The lesion involves the leg. The subject is 40–49, male. The photo was captured at an angle.
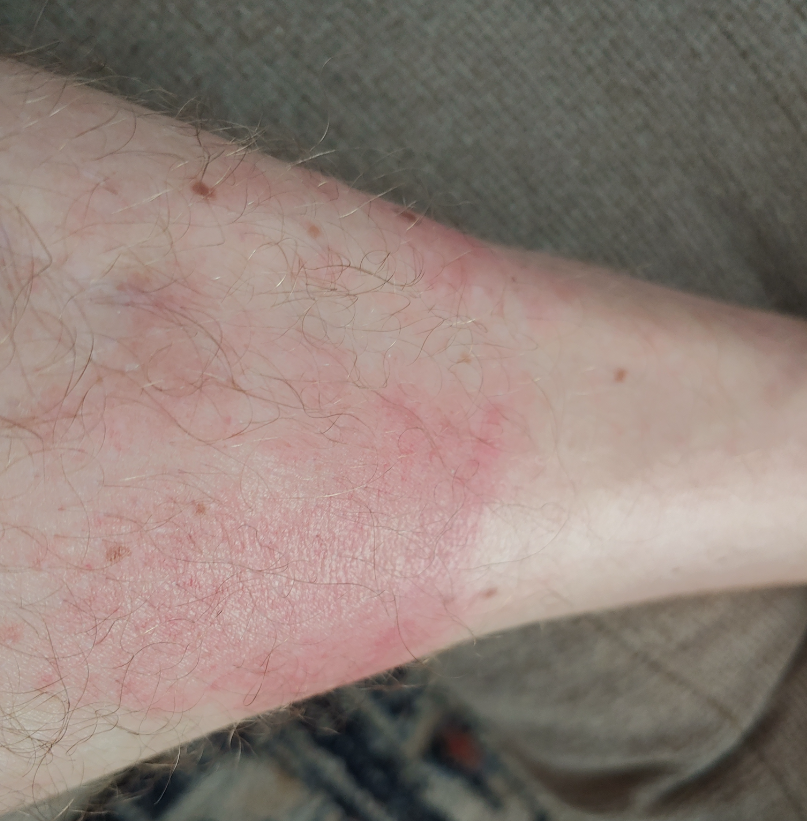Q: What conditions are considered?
A: the favored diagnosis is Allergic Contact Dermatitis; also raised was Irritant Contact Dermatitis